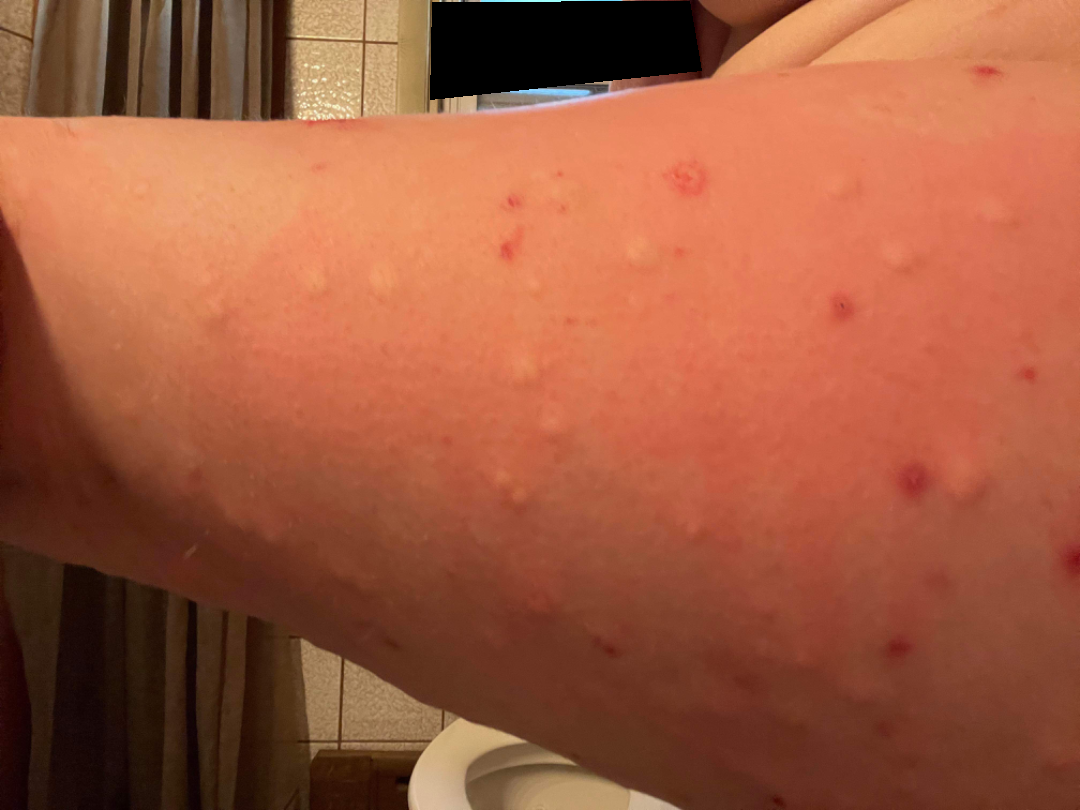– shot type — at an angle
– impression — the differential, in no particular order, includes Pityriasis lichenoides, Scabies and Insect Bite